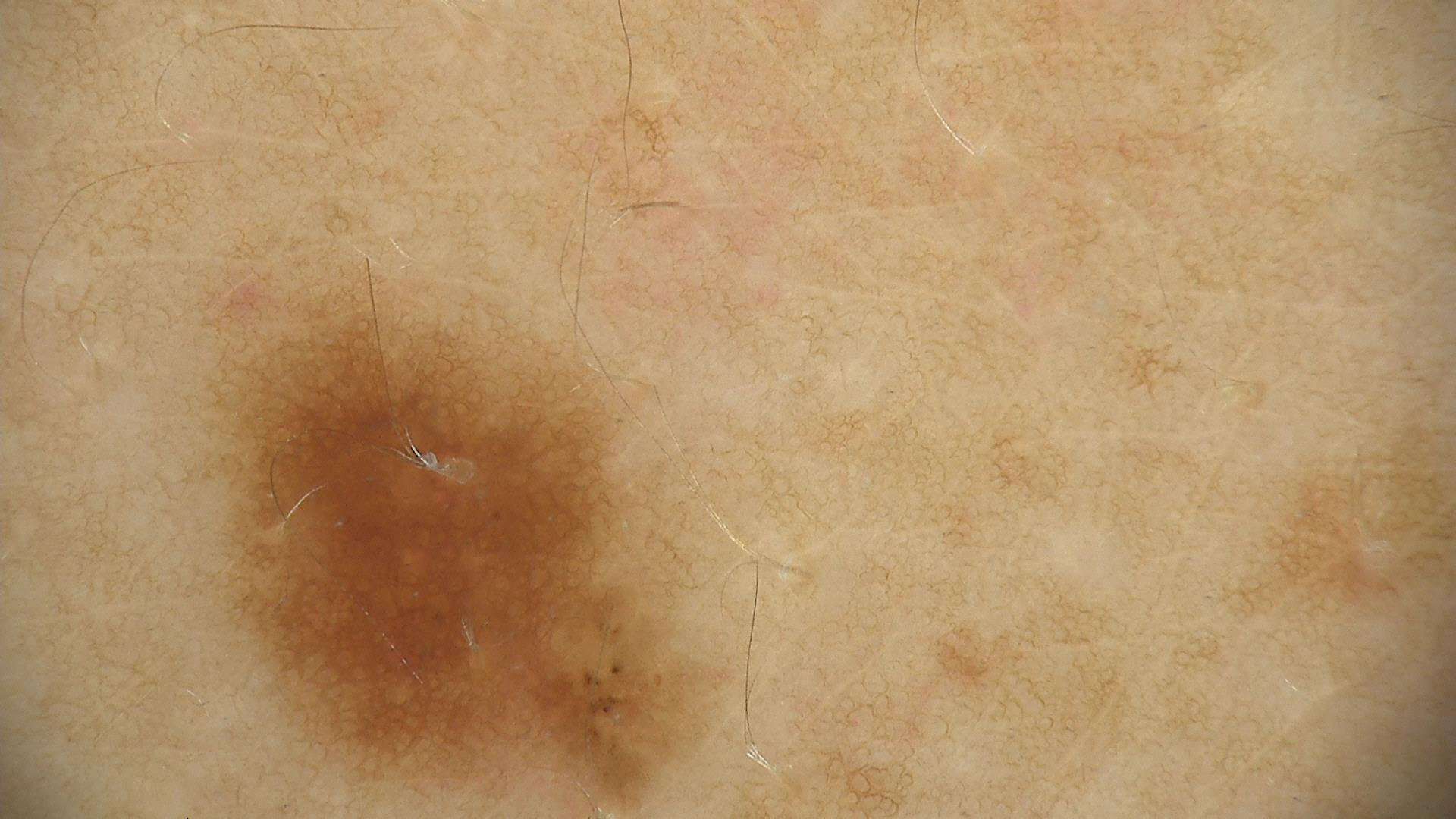image type=dermatoscopy
label=dysplastic junctional nevus (expert consensus)